A dermoscopic close-up of a skin lesion · a male patient, aged approximately 50: 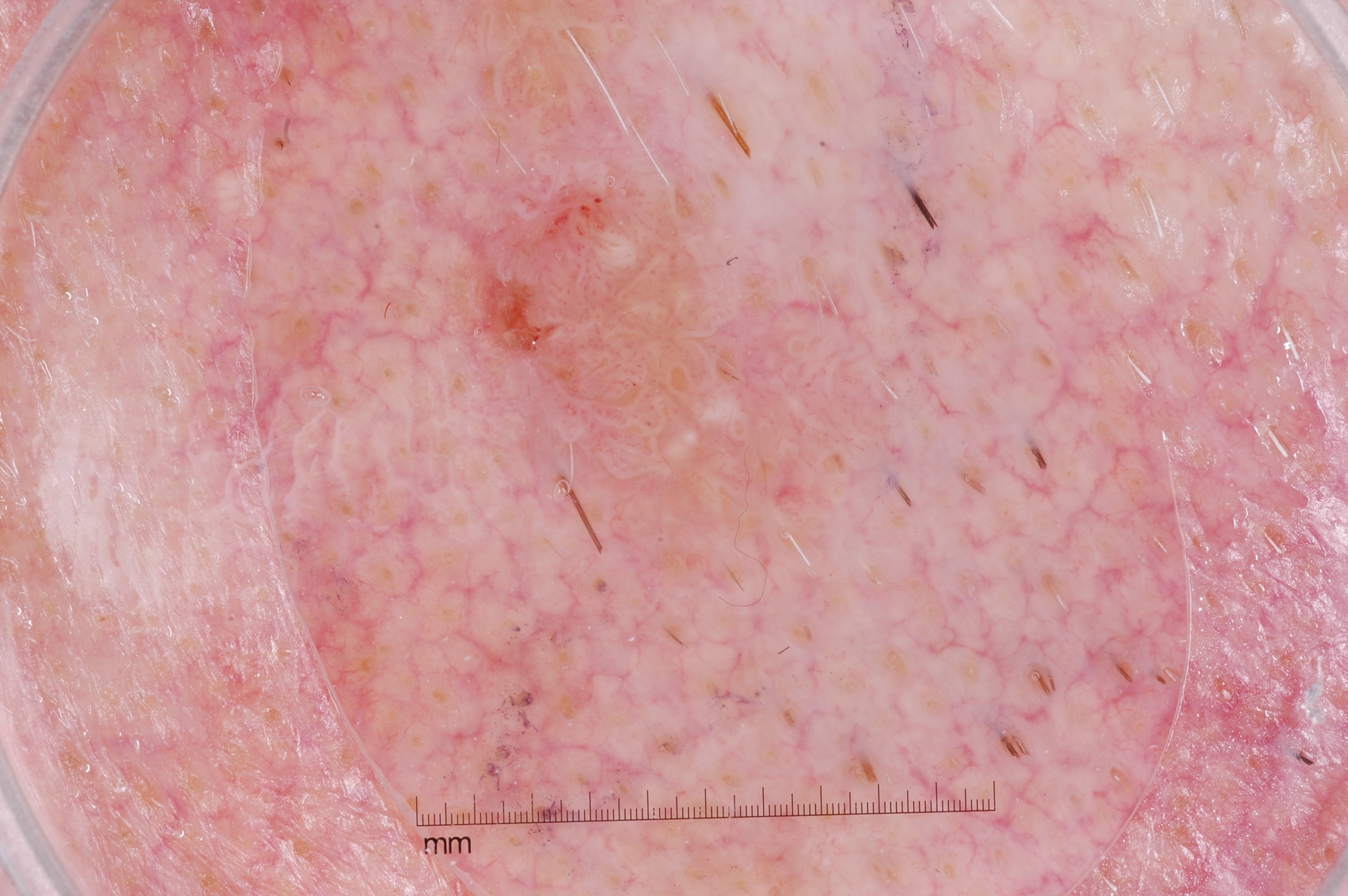In (x1, y1, x2, y2) order, the visible lesion spans box(354, 170, 833, 590).
On dermoscopy, the lesion shows milia-like cysts; no pigment network, streaks, or negative network.
Clinically diagnosed as a seborrheic keratosis.